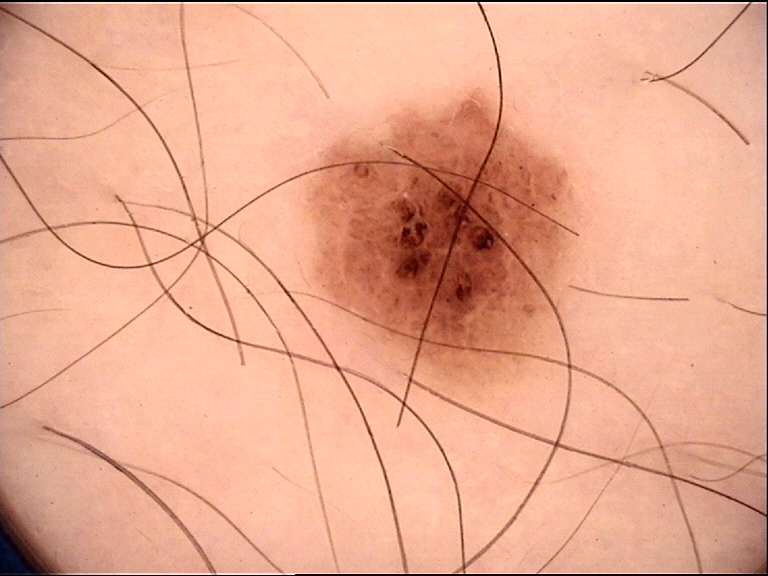Consistent with a dysplastic compound nevus.